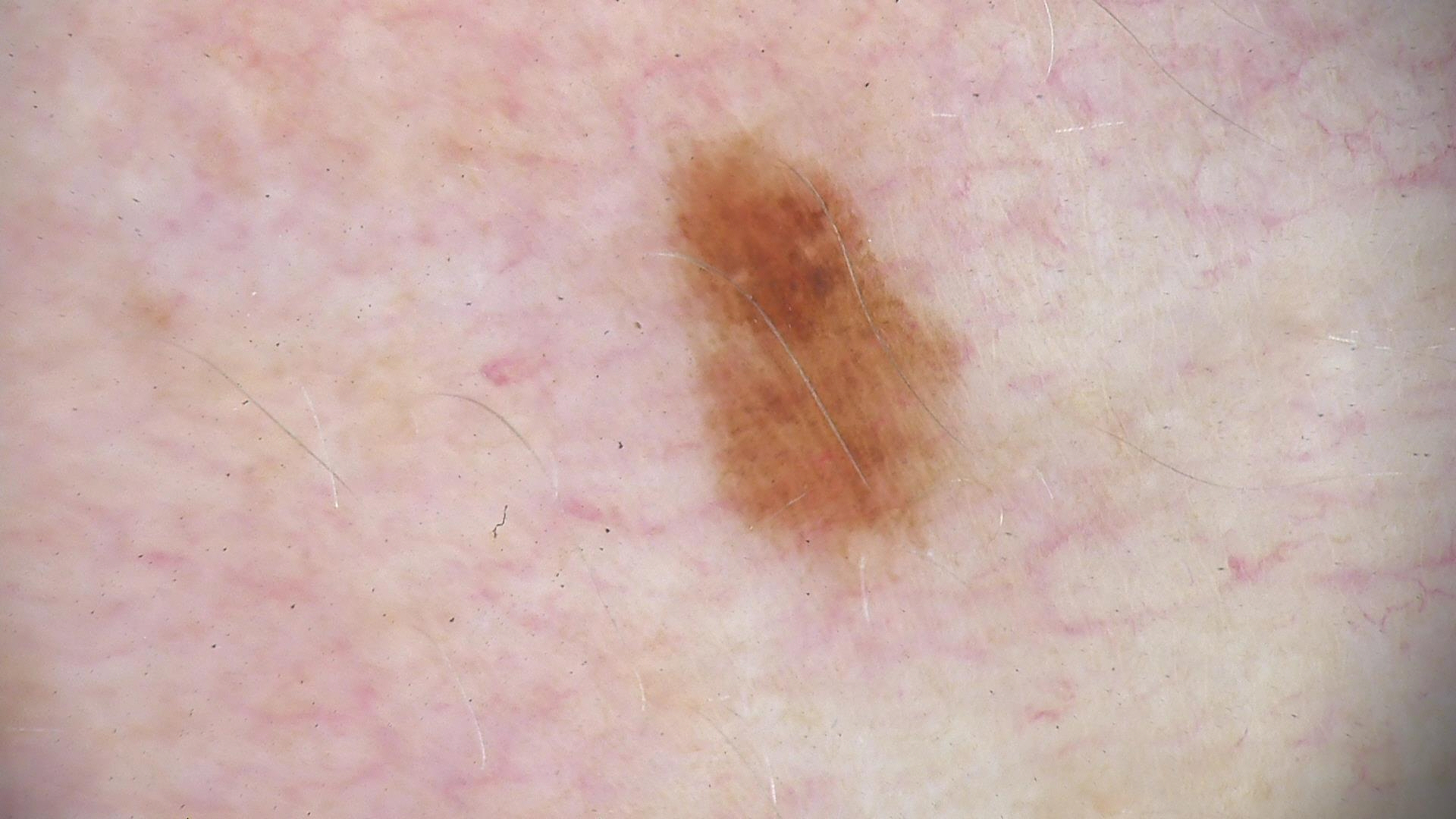imaging=dermatoscopy | label=acral dysplastic junctional nevus (expert consensus).